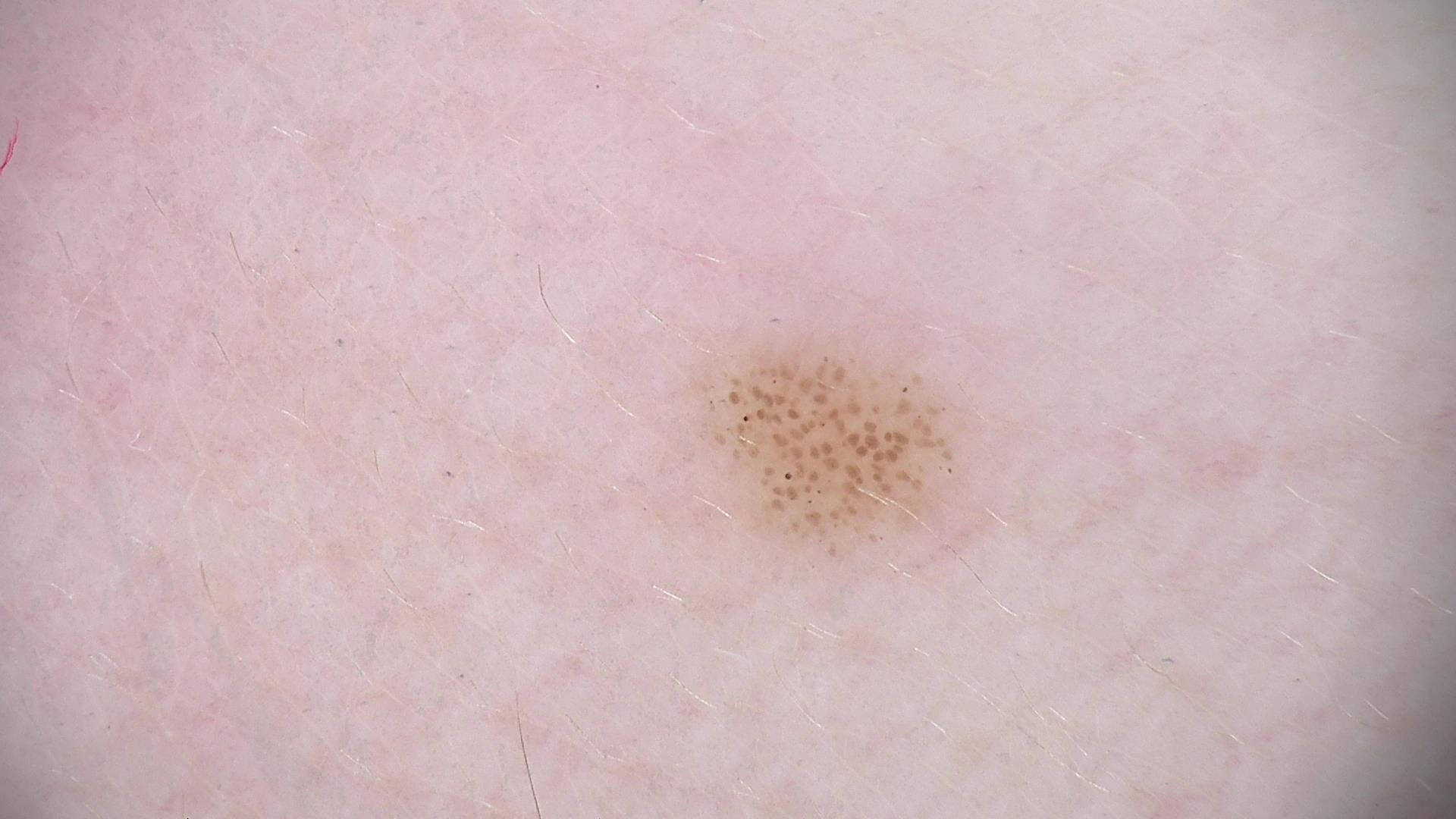Dermoscopy of a skin lesion.
Diagnosed as a dysplastic junctional nevus.